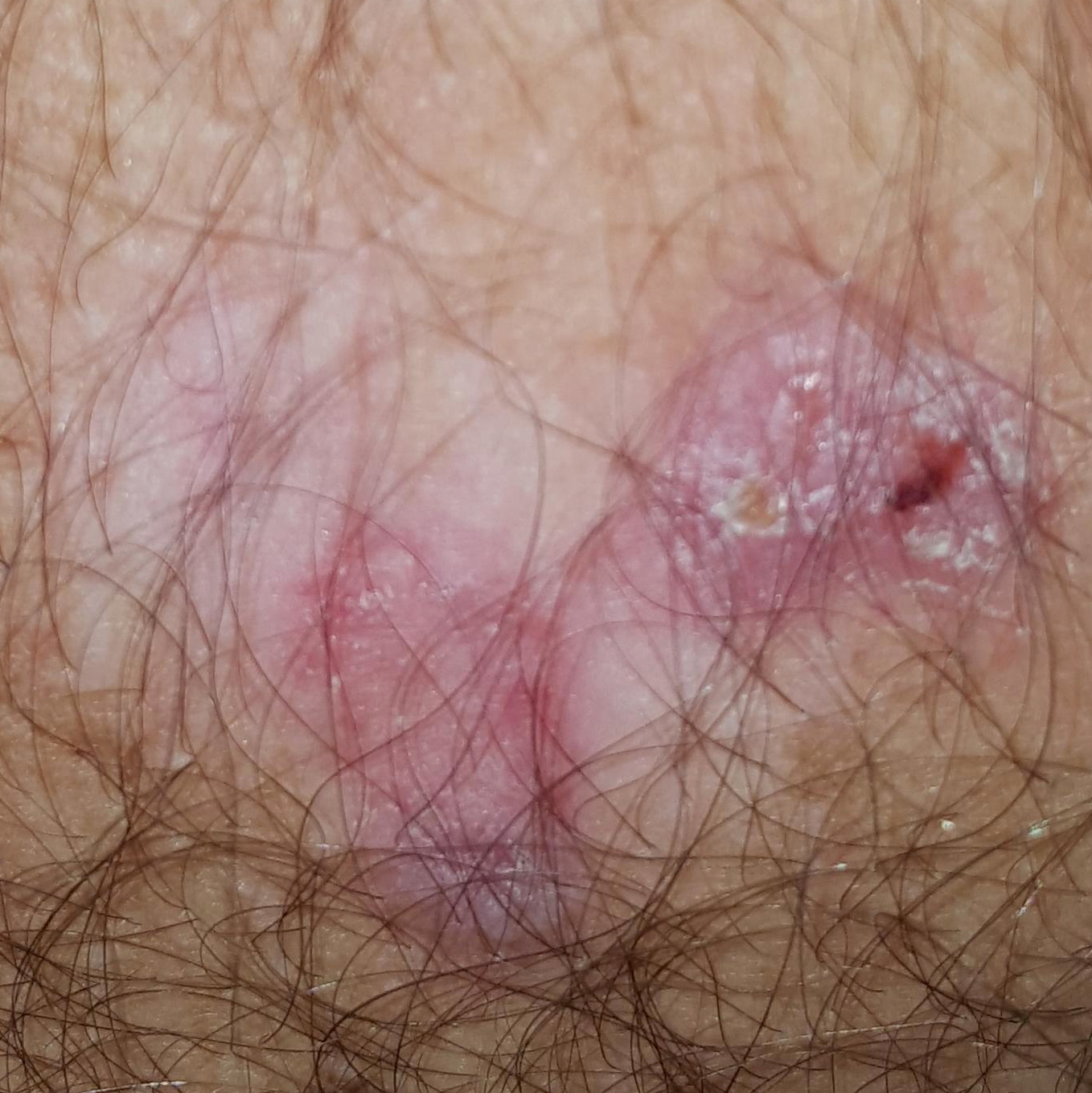The chart records prior malignancy (patient or family), alcohol use, no pesticide exposure, and no prior skin cancer (patient or family). The lesion is located on the back. Measuring about 30 × 20 mm. The patient reports that the lesion has grown, has bled, and itches. Histopathologically confirmed as a basal cell carcinoma.